A dermoscopic close-up of a skin lesion.
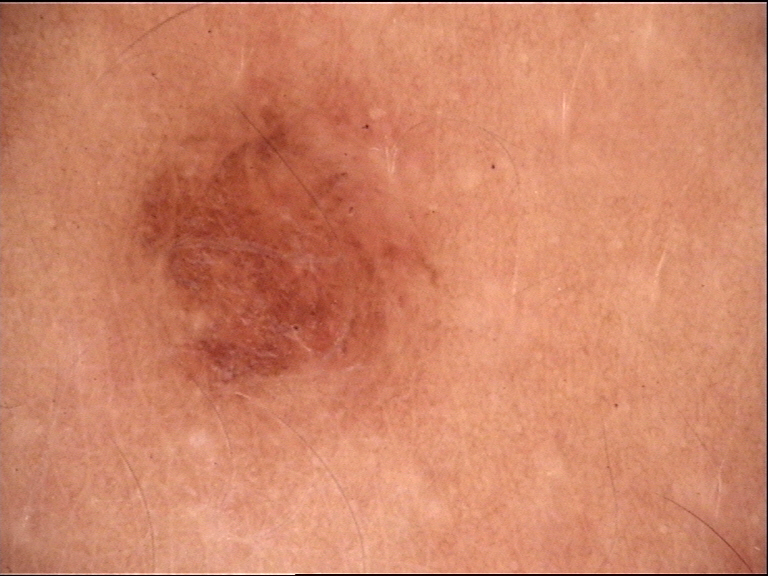Conclusion:
Consistent with a dysplastic junctional nevus.